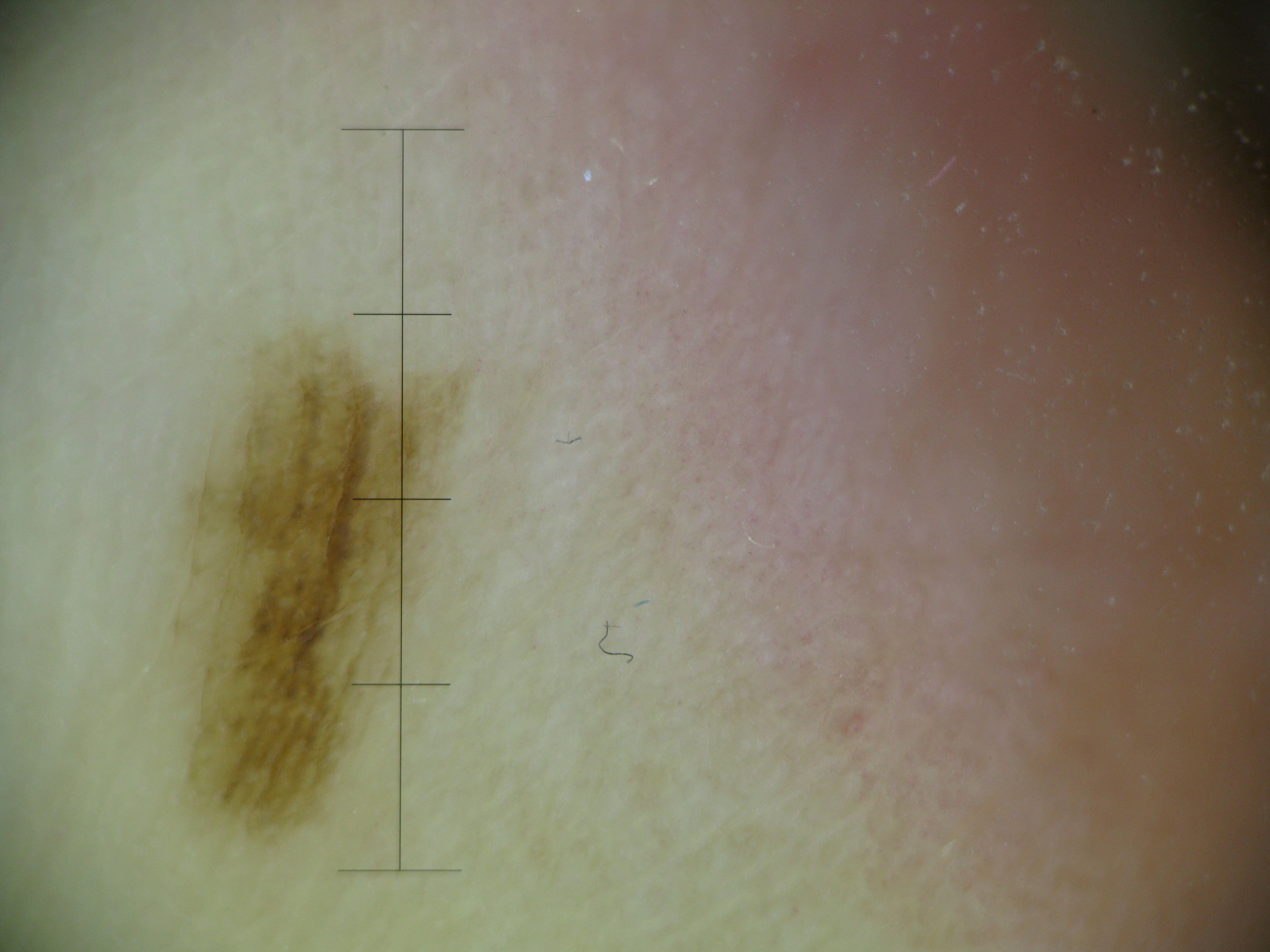Classified as a benign lesion — an acral dysplastic junctional nevus.